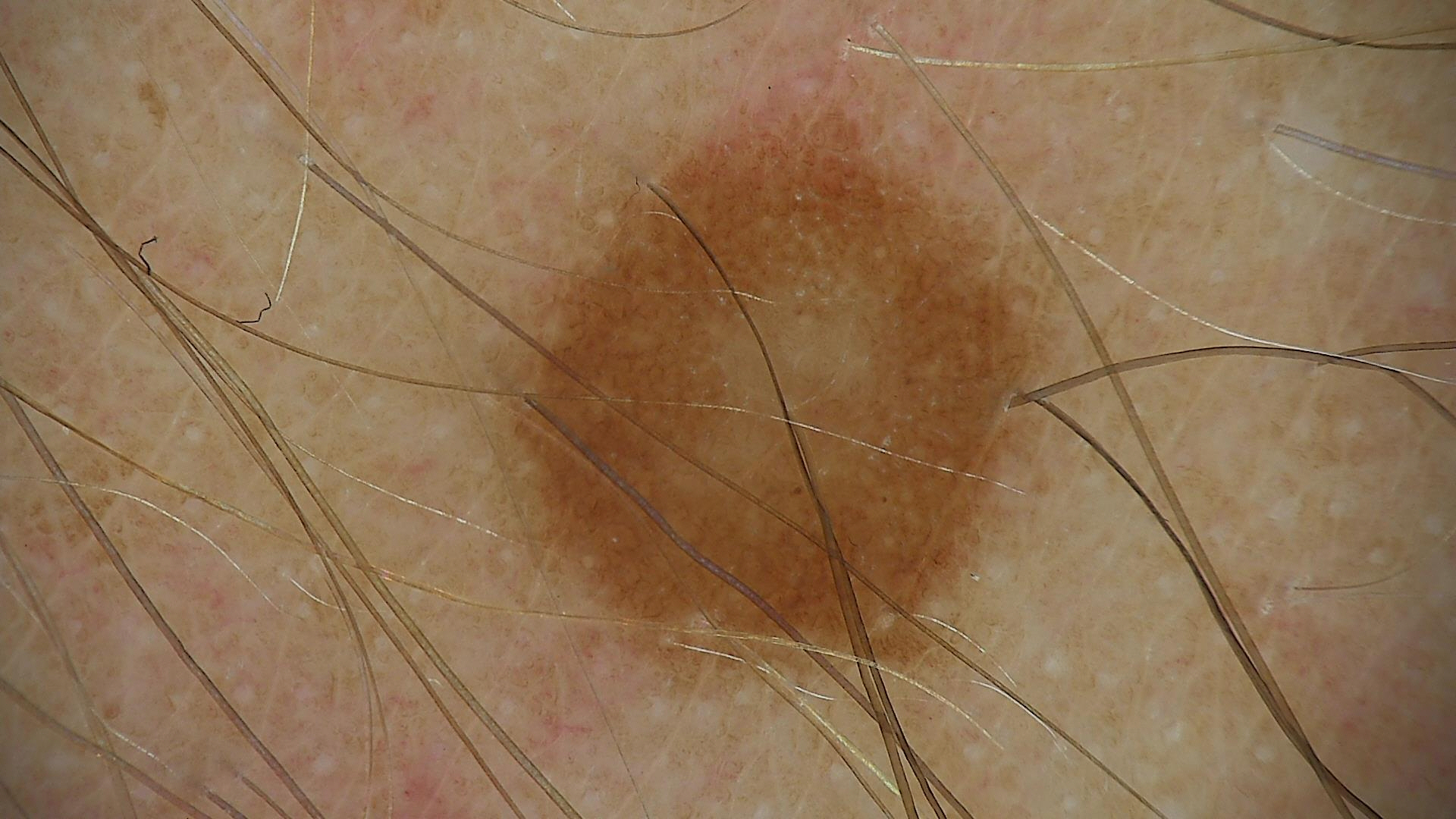A dermatoscopic image of a skin lesion. Consistent with a benign lesion — a dysplastic junctional nevus.